This is a dermoscopic photograph of a skin lesion.
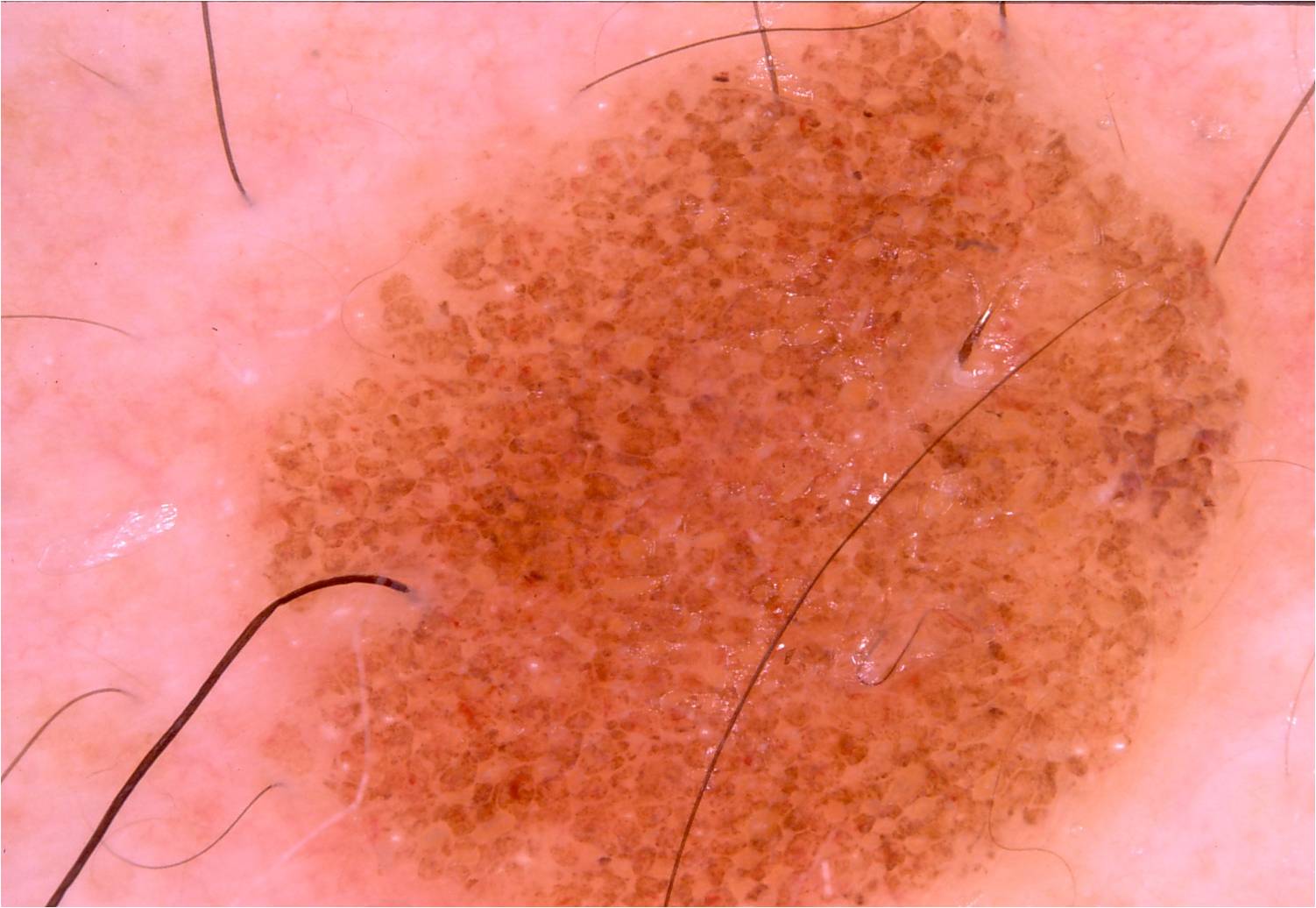The lesion is bounded by box(245, 2, 1255, 906).
Dermoscopic examination shows globules, with no pigment network, milia-like cysts, streaks, or negative network.
Clinically diagnosed as a melanocytic nevus.